A skin lesion imaged with a dermatoscope.
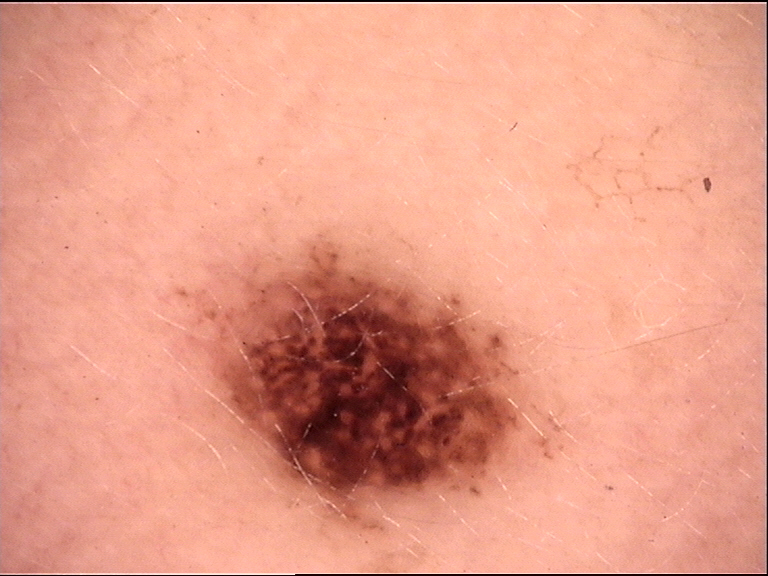This is a banal lesion. Classified as a compound nevus.